A dermoscopy image of a single skin lesion: 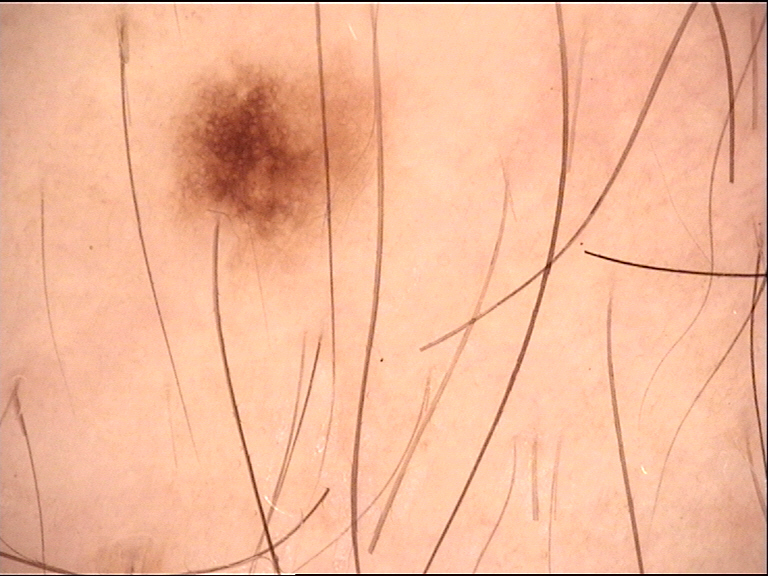The diagnosis was a dysplastic junctional nevus.